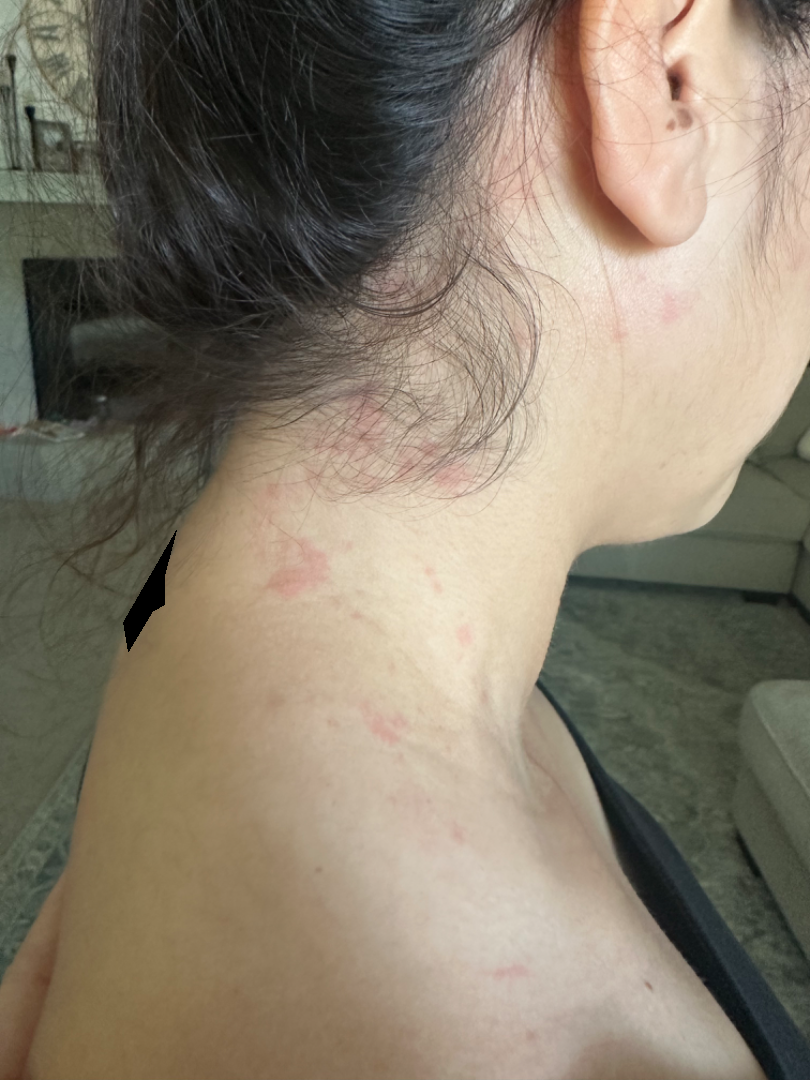Findings:
The skin findings could not be characterized from the image.
Background:
The affected area is the head or neck. The photo was captured at a distance.